A female subject about 35 years old, a dermoscopic view of a skin lesion:
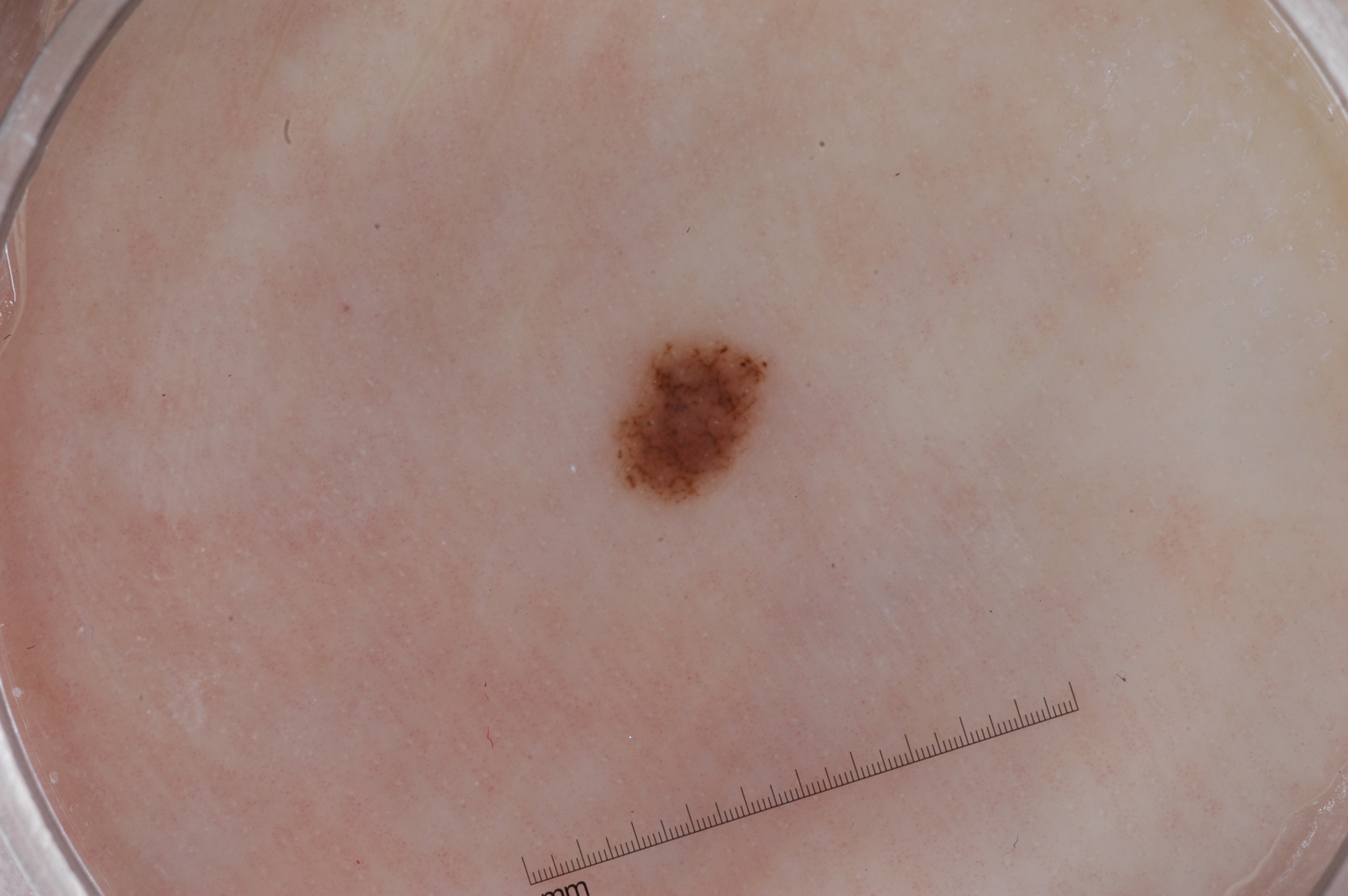Dermoscopic review identifies pigment network; no milia-like cysts, streaks, or negative network. As (left, top, right, bottom), the lesion occupies the region [601,331,782,516]. The lesion covers approximately 2% of the dermoscopic field. The clinical diagnosis was a melanocytic nevus.